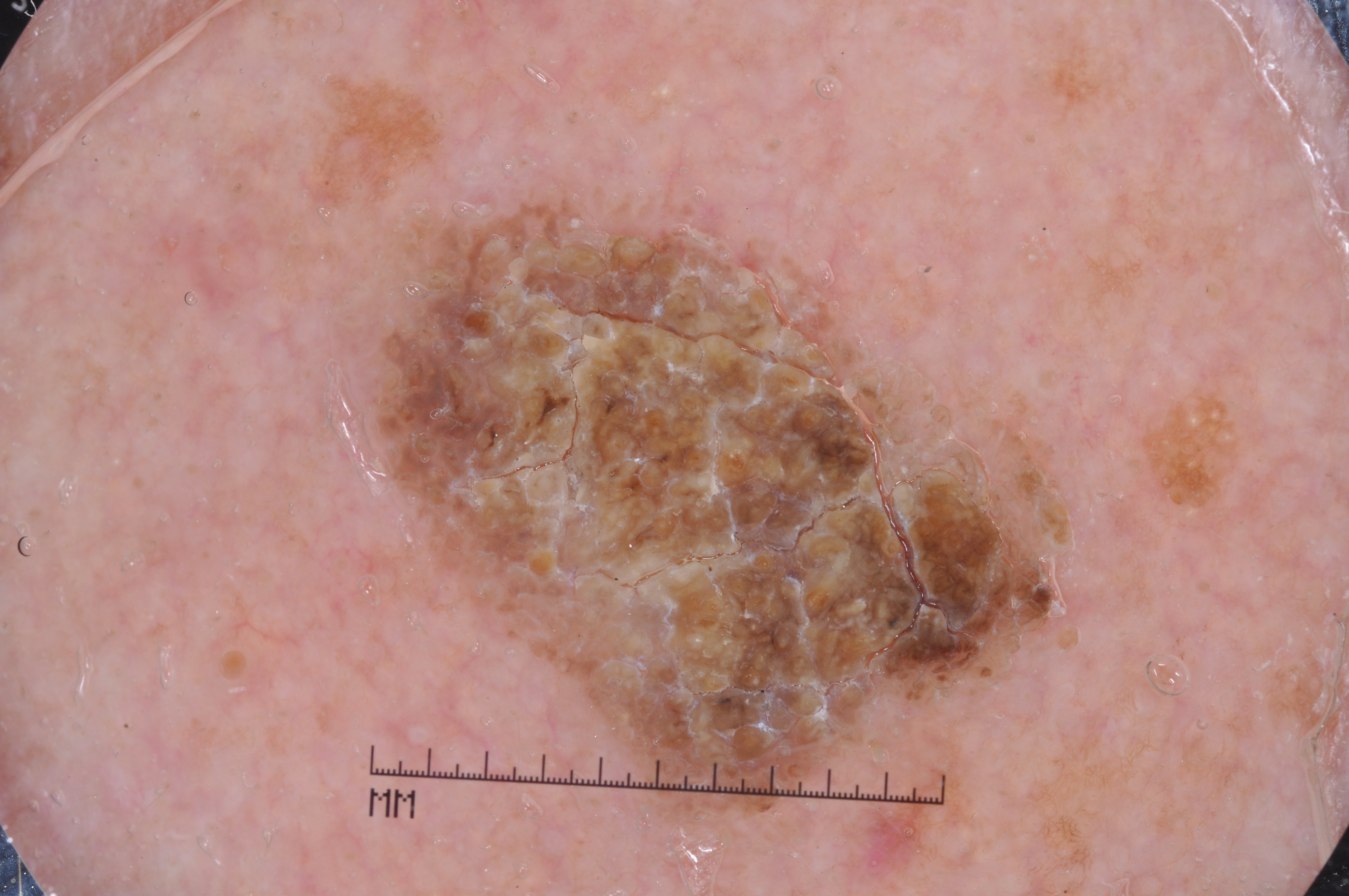{"image": {"modality": "dermoscopy"}, "lesion_location": {"bbox_xyxy": [369, 203, 1054, 819]}, "diagnosis": {"name": "seborrheic keratosis", "malignancy": "benign", "lineage": "keratinocytic", "provenance": "clinical"}}